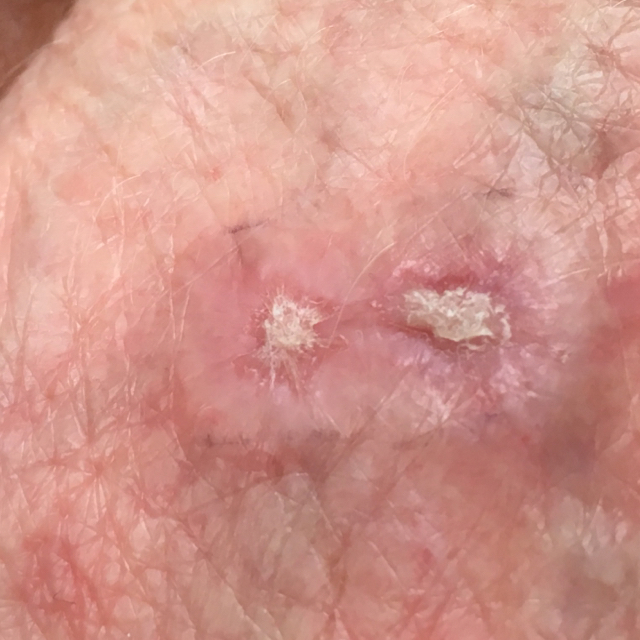Findings: A clinical photograph of a skin lesion. A subject age 58. The lesion involves a hand. The patient reports that the lesion is elevated and itches. Impression: Expert review favored an actinic keratosis.